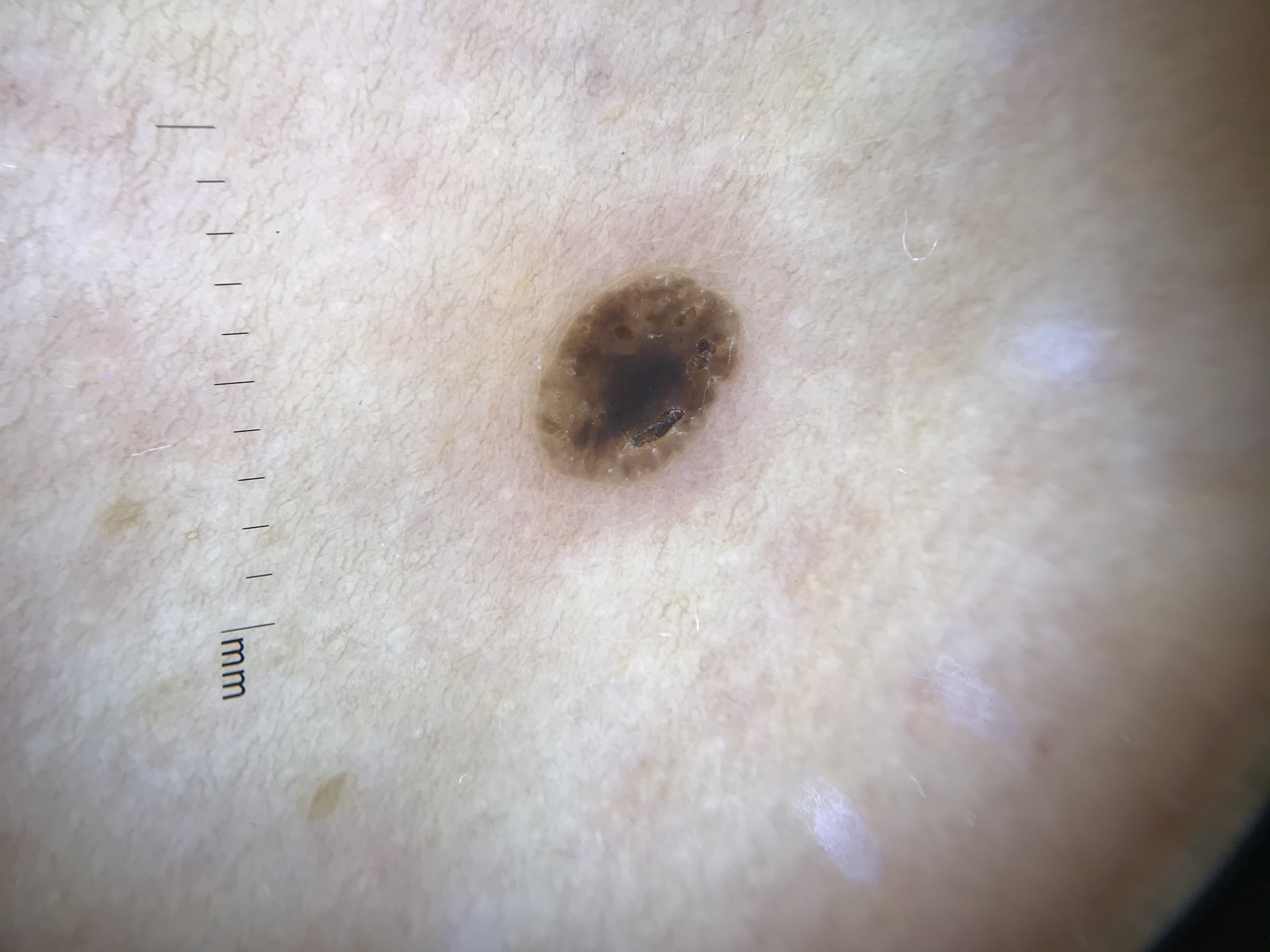{
  "diagnosis": {
    "name": "seborrheic keratosis",
    "code": "sk",
    "malignancy": "benign",
    "super_class": "non-melanocytic",
    "confirmation": "expert consensus"
  }
}